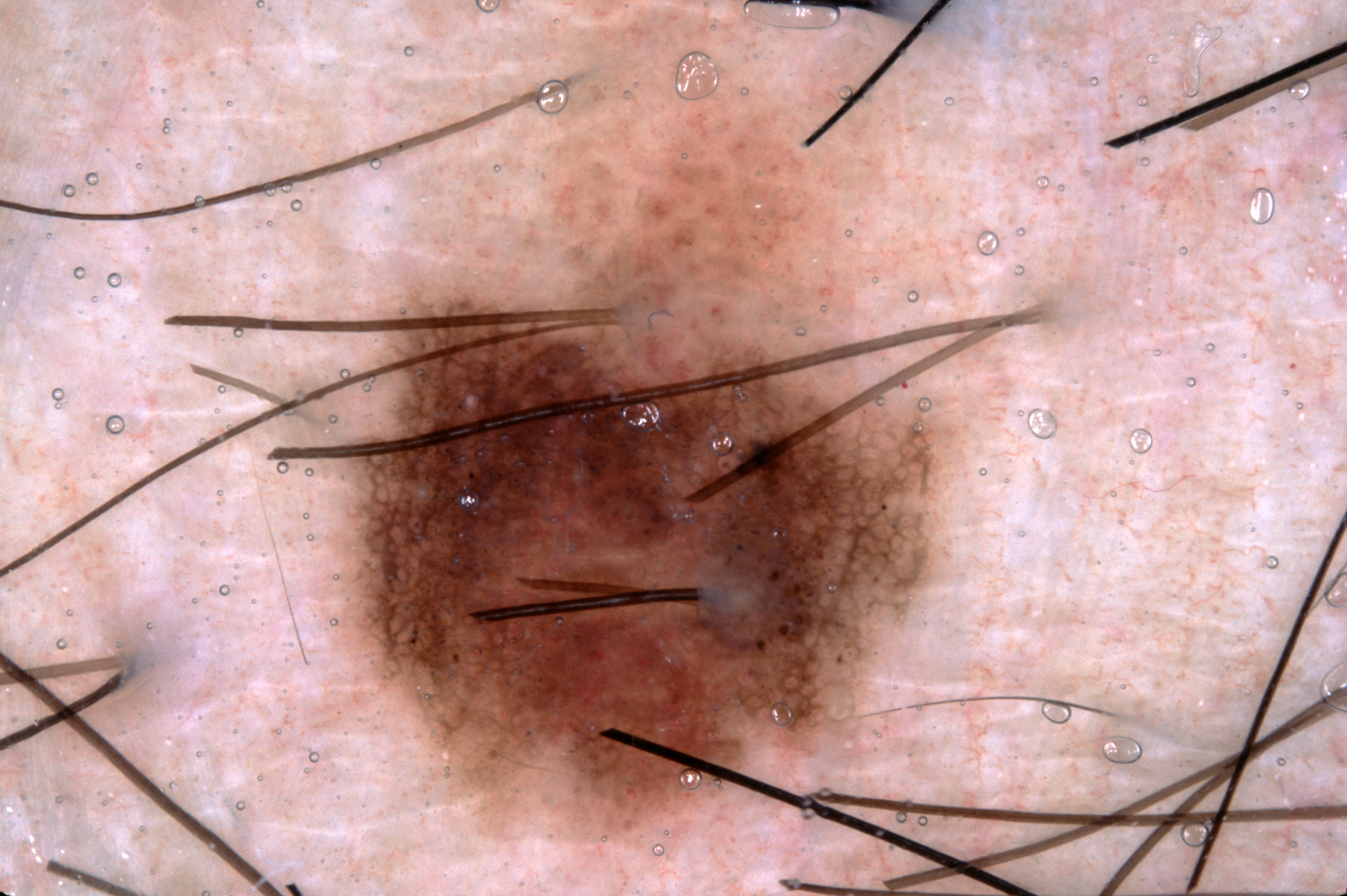patient: male, about 30 years old; image type: dermoscopy; lesion location: (347, 126, 958, 833); dermoscopic pattern: pigment network; lesion extent: ~25% of the field; assessment: a melanocytic nevus.